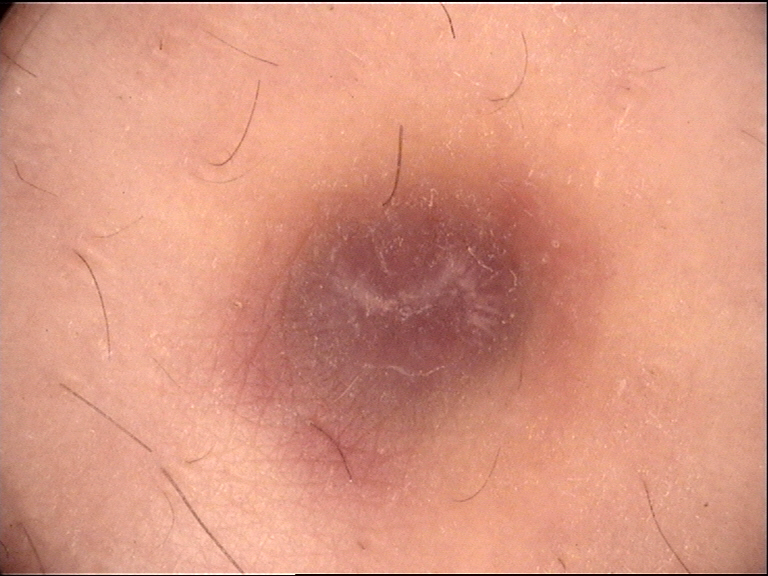<case>
  <diagnosis>
    <name>dermatofibroma</name>
    <code>df</code>
    <malignancy>benign</malignancy>
    <super_class>non-melanocytic</super_class>
    <confirmation>expert consensus</confirmation>
  </diagnosis>
</case>